A dermoscopy image of a single skin lesion.
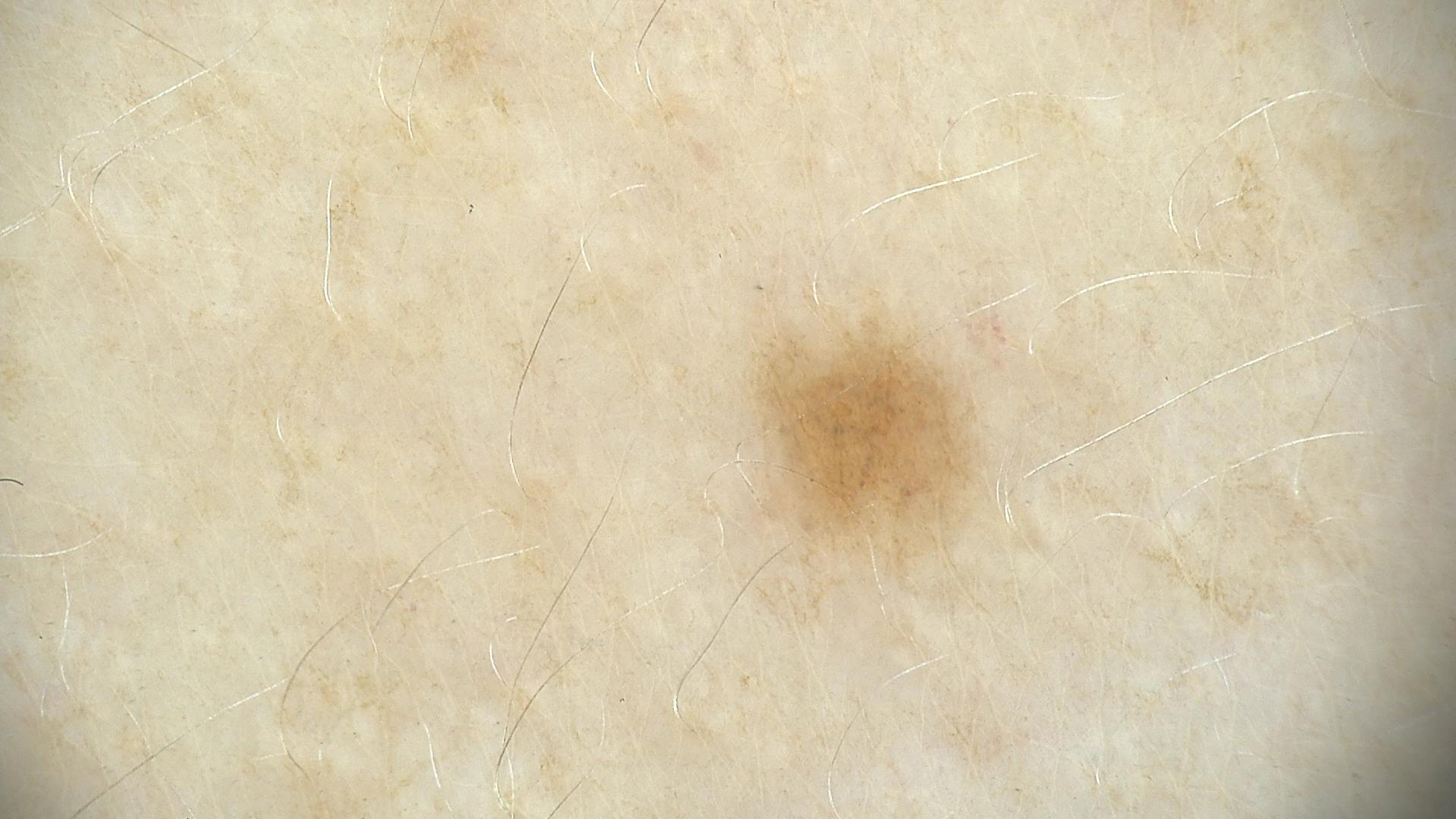The diagnosis was a banal lesion — a junctional nevus.